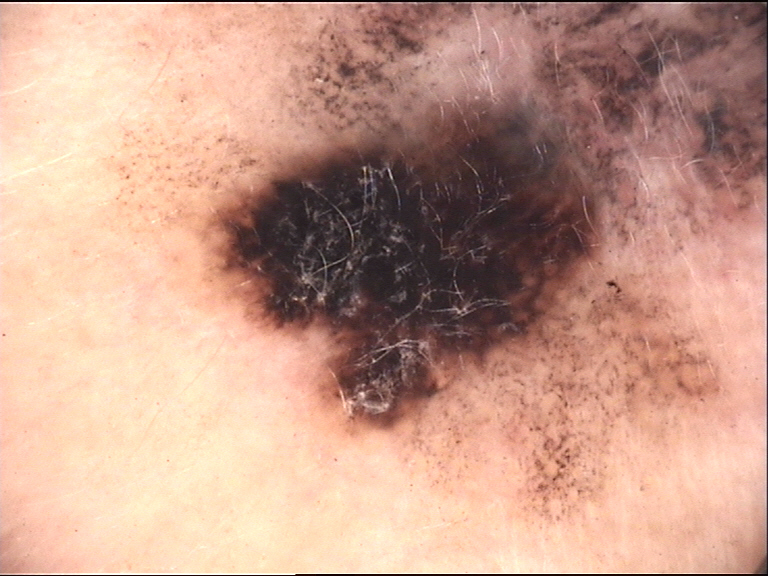Confirmed on histopathology as a lentigo maligna melanoma.